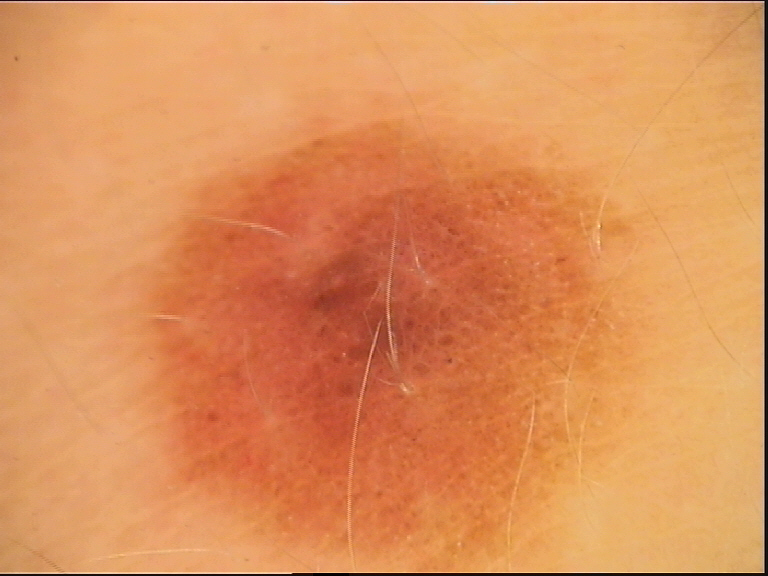| field | value |
|---|---|
| subtype | banal |
| class | compound nevus (expert consensus) |